A subject aged 35 · a clinical photograph of a skin lesion — 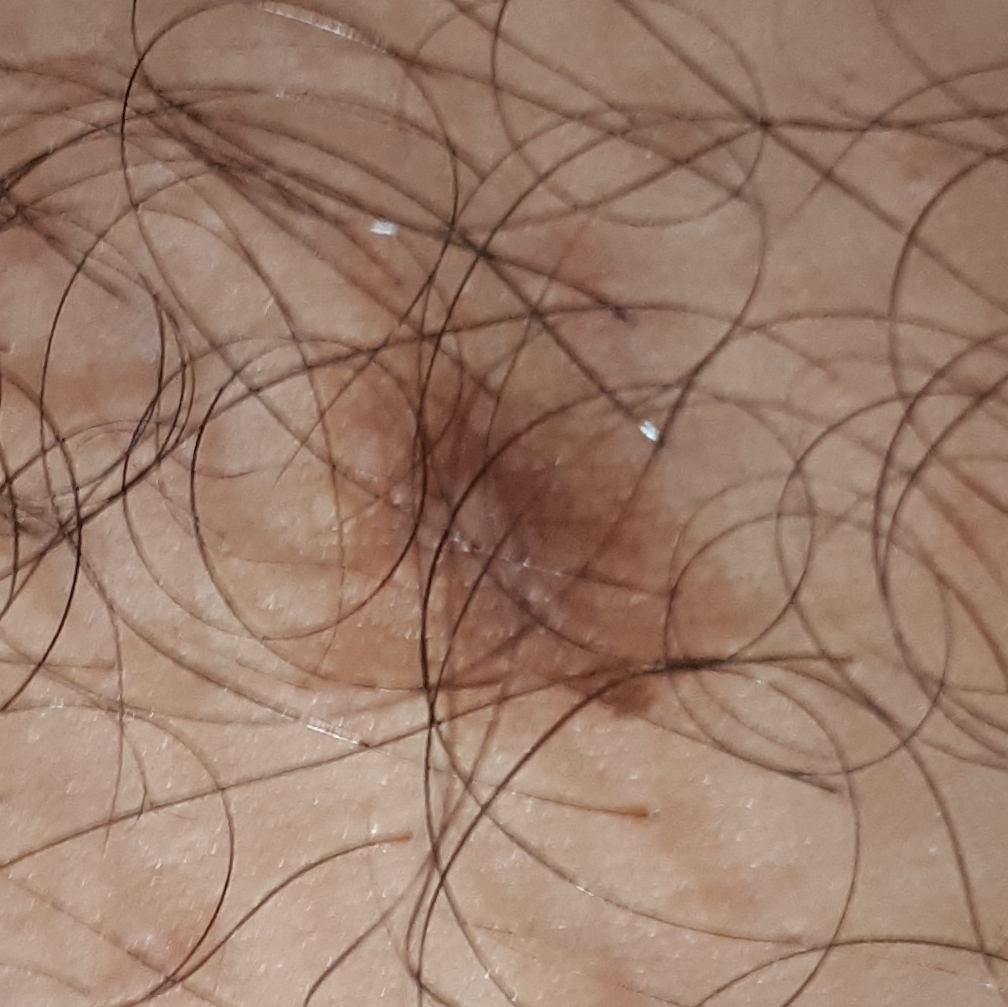The lesion is located on a thigh.
By the patient's account, the lesion has grown and is elevated, but has not changed and has not bled.
The consensus clinical diagnosis was a nevus.